A dermoscopic image of a skin lesion, a female patient aged around 35.
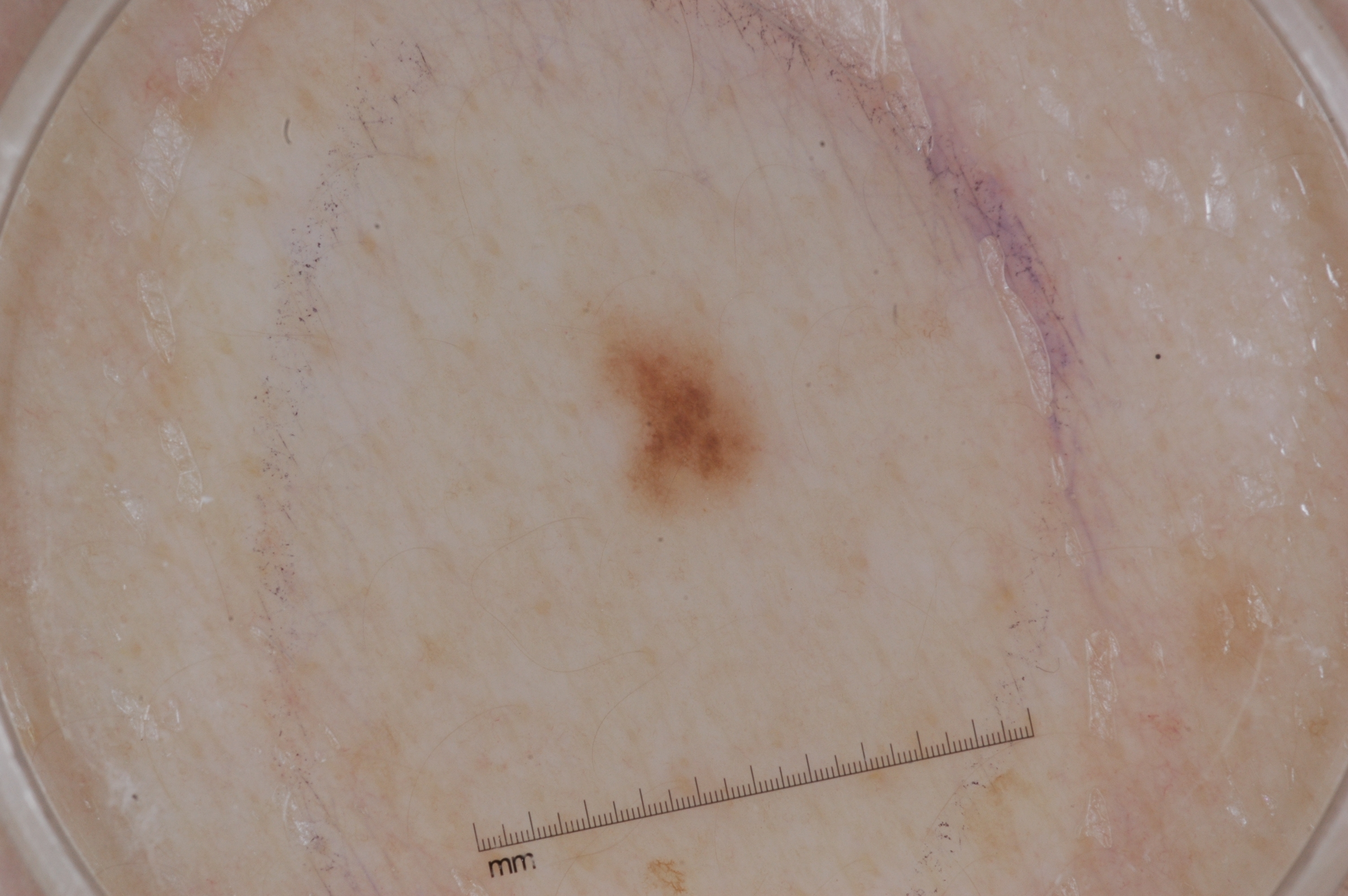Findings:
The lesion spans (590, 322, 758, 511). The dermoscopic pattern shows pigment network; no negative network, streaks, or milia-like cysts.
Impression:
Expert review diagnosed this as a melanocytic nevus.